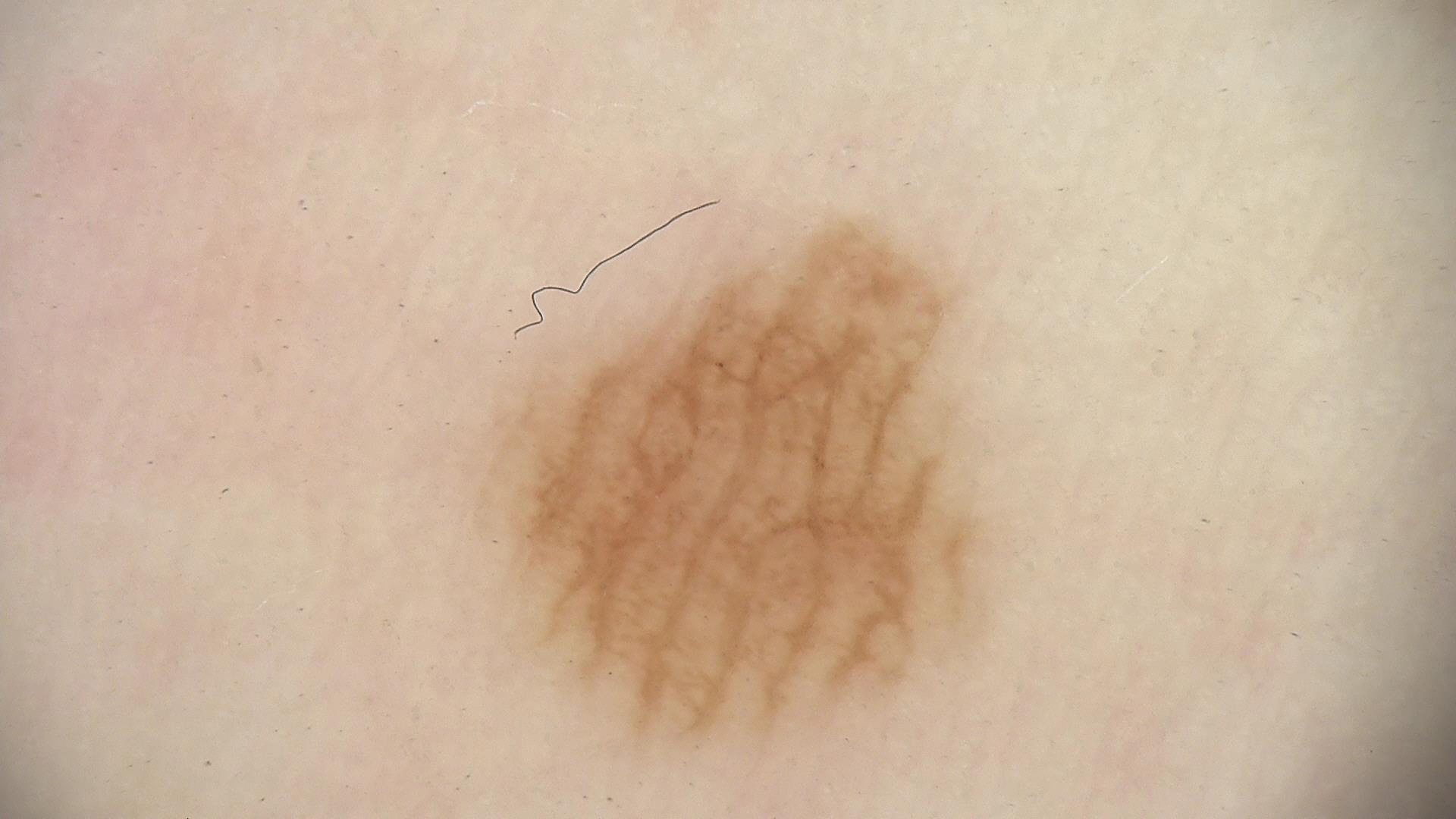A dermoscopic photograph of a skin lesion.
The diagnostic label was an acral dysplastic junctional nevus.